The lesion is described as rough or flaky · self-categorized by the patient as acne · this is a close-up image · the front of the torso is involved · present for less than one week · the patient did not report lesion symptoms · the subject is a male aged 18–29.
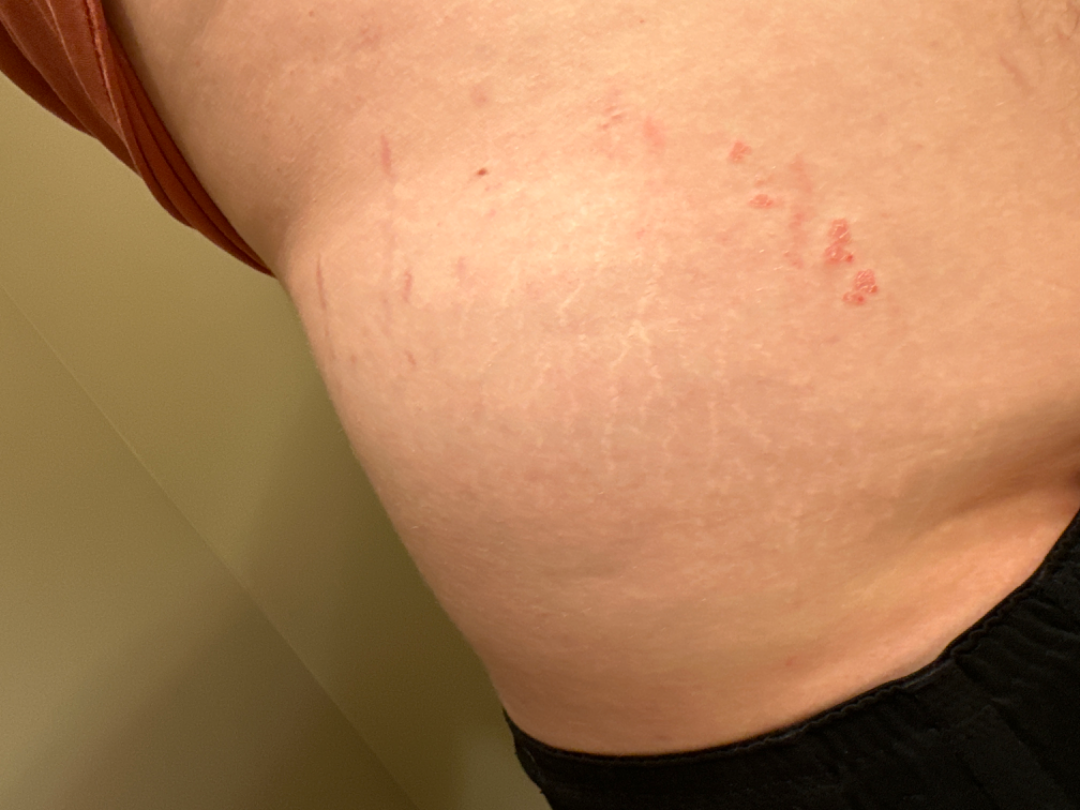Review: No differential diagnosis could be assigned on photographic review.